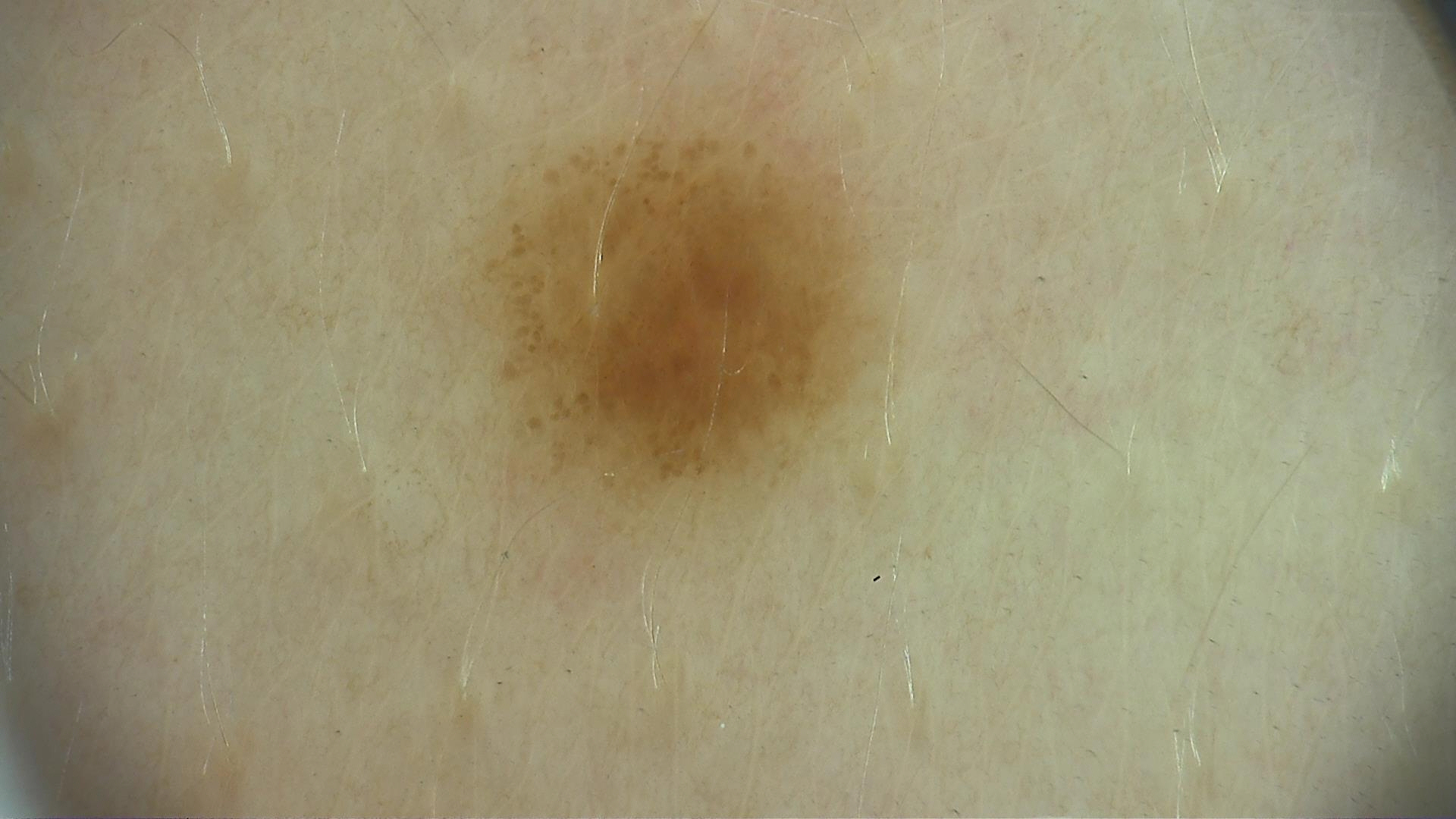diagnosis: dysplastic junctional nevus (expert consensus).